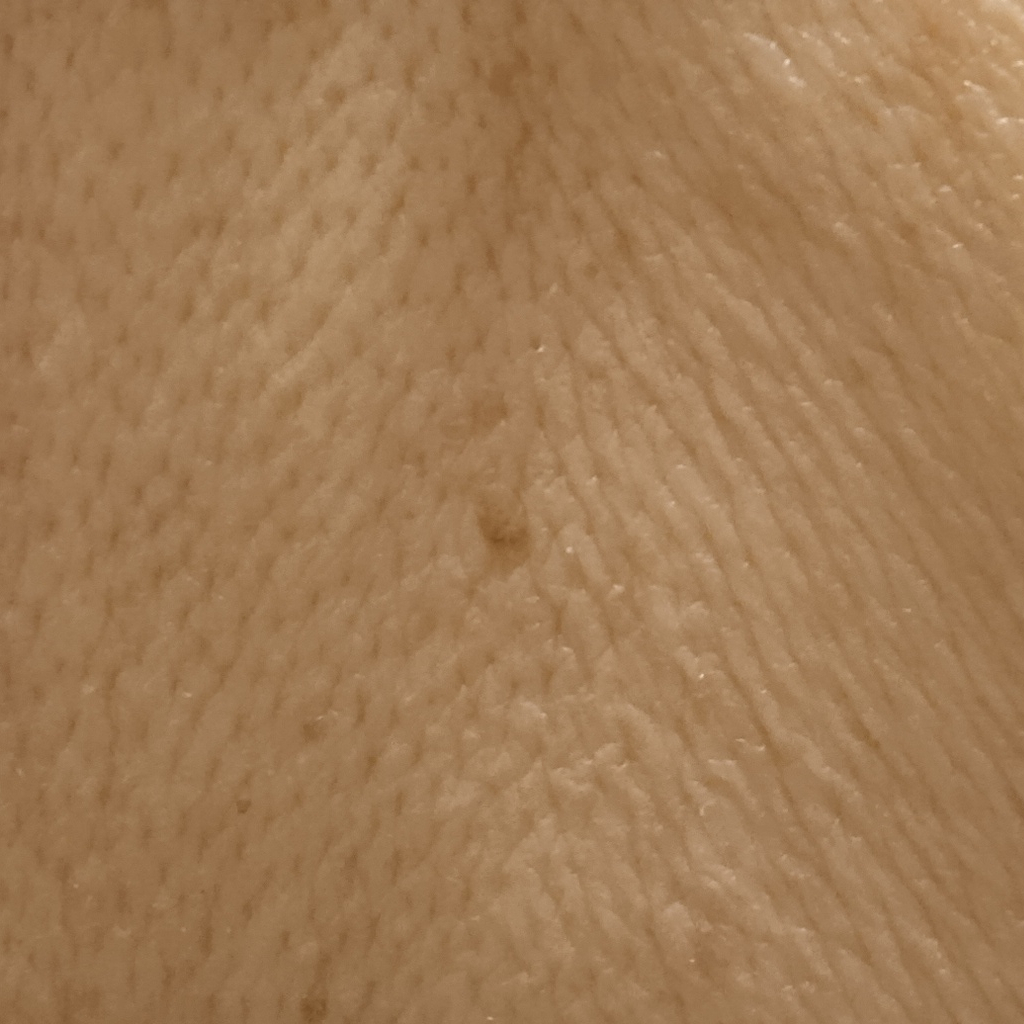referral = research study (no referral diagnosis), location = an arm, size = 6.1 mm, assessment = melanocytic nevus (dermatologist consensus).